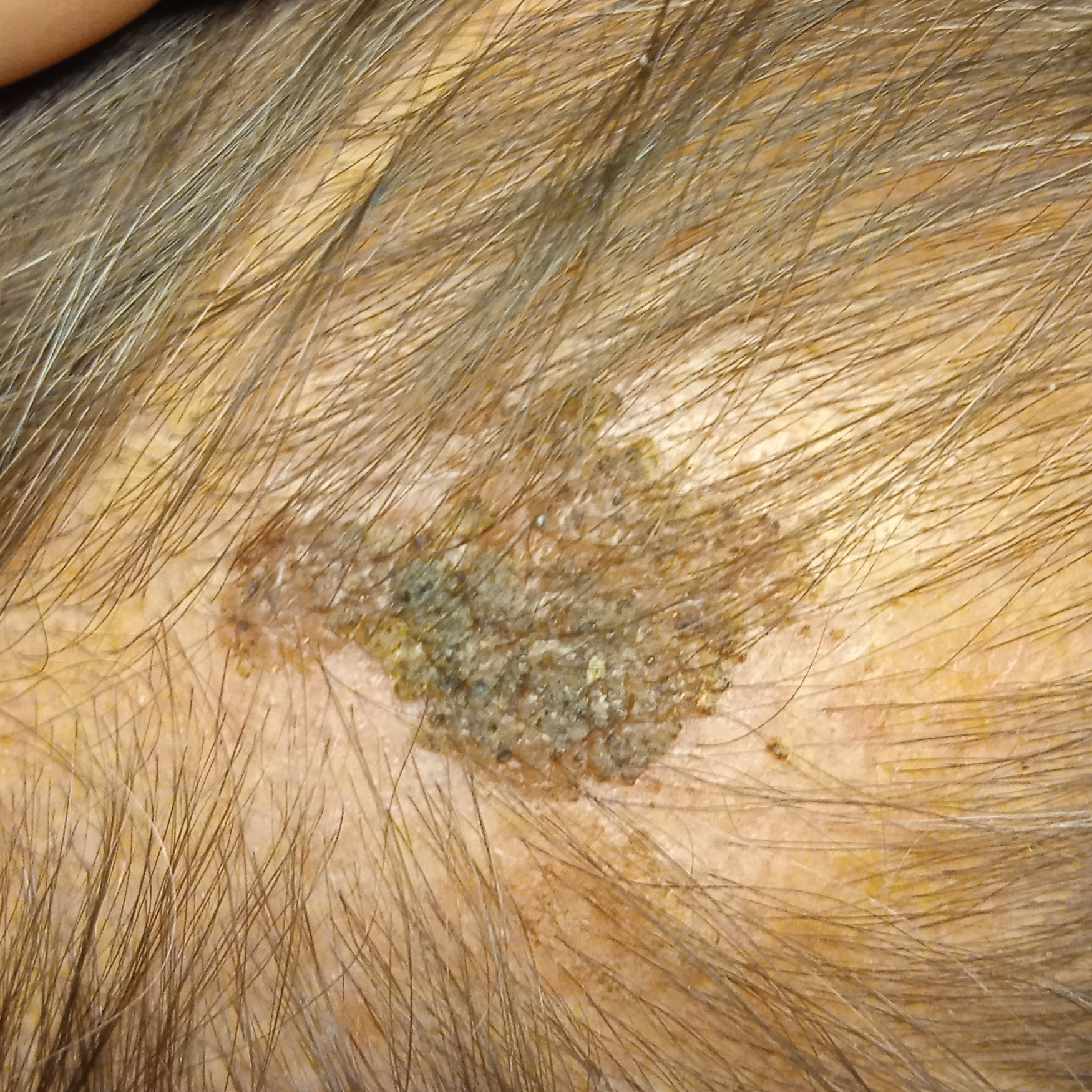• imaging · clinical photograph
• clinical context · research study (no referral diagnosis)
• nevus count · a moderate number of melanocytic nevi
• subject · male, aged 72
• location · the head
• lesion size · 19.2 mm
• diagnosis · seborrheic keratosis (dermatologist consensus)